The photograph is a close-up of the affected area; located on the leg: 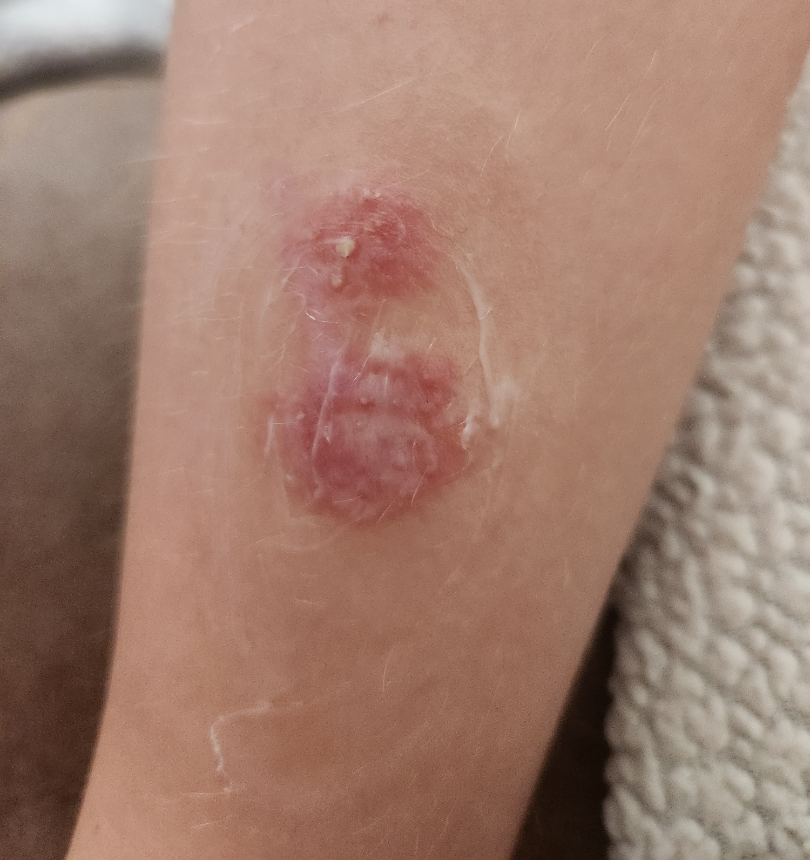Q: What was the assessment?
A: indeterminate